A male patient aged around 50; a dermoscopy image of a single skin lesion.
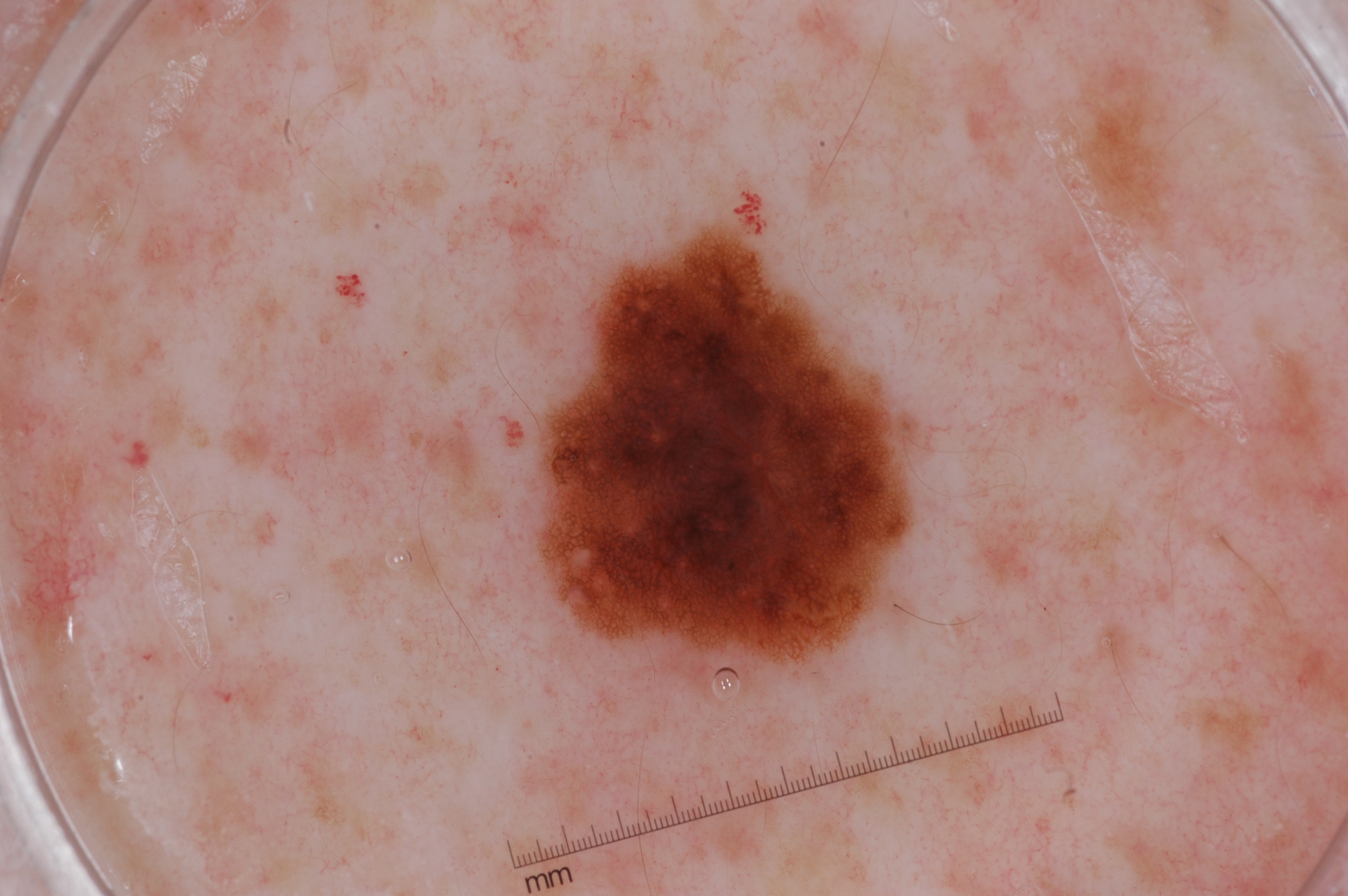Dermoscopic examination shows pigment network.
The lesion takes up about 10% of the image.
Lesion location: x1=548, y1=231, x2=906, y2=665.
The diagnostic assessment was a melanocytic nevus.